A dermoscopic image of a skin lesion.
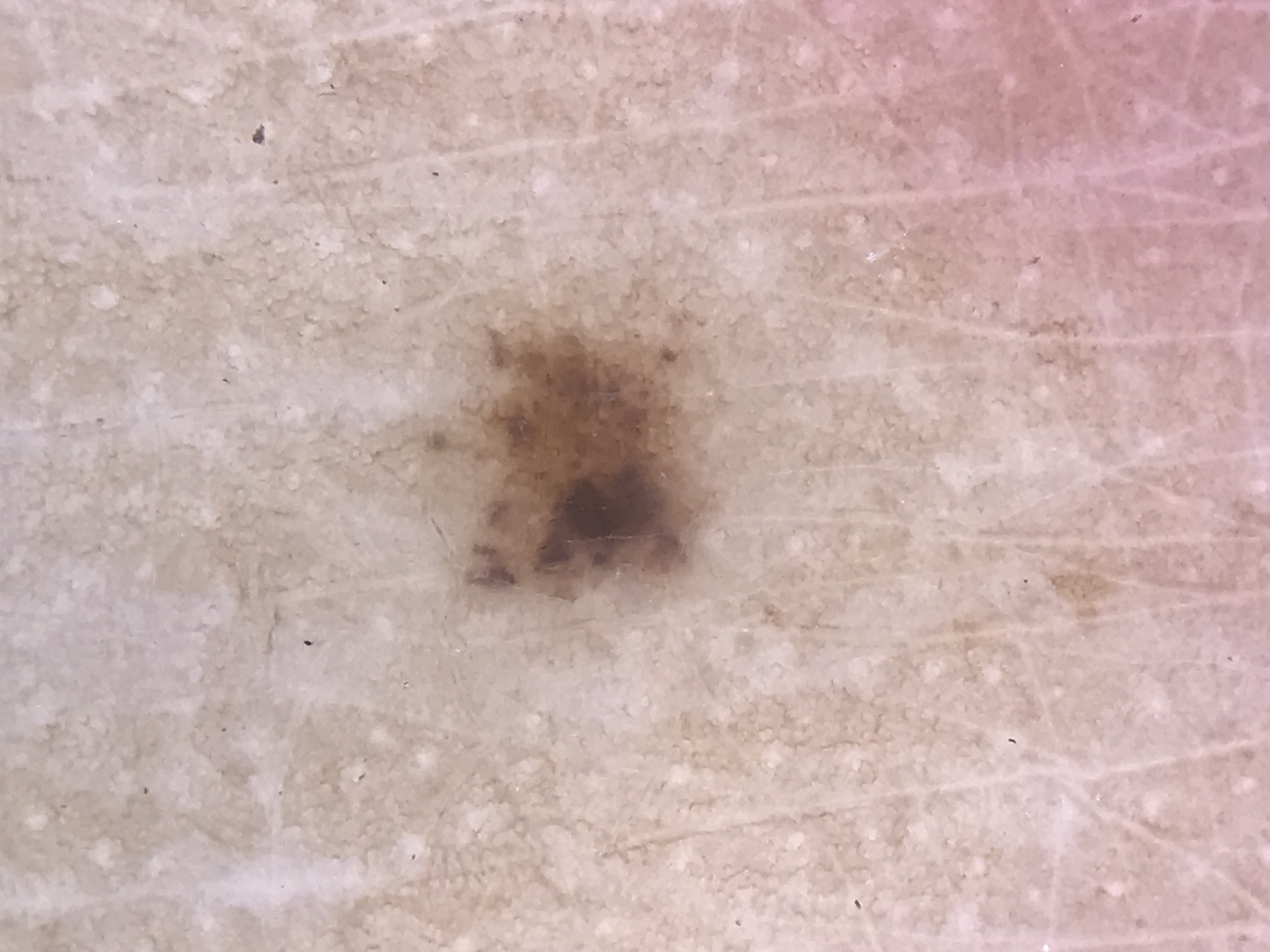Conclusion:
Diagnosed as a dysplastic junctional nevus.